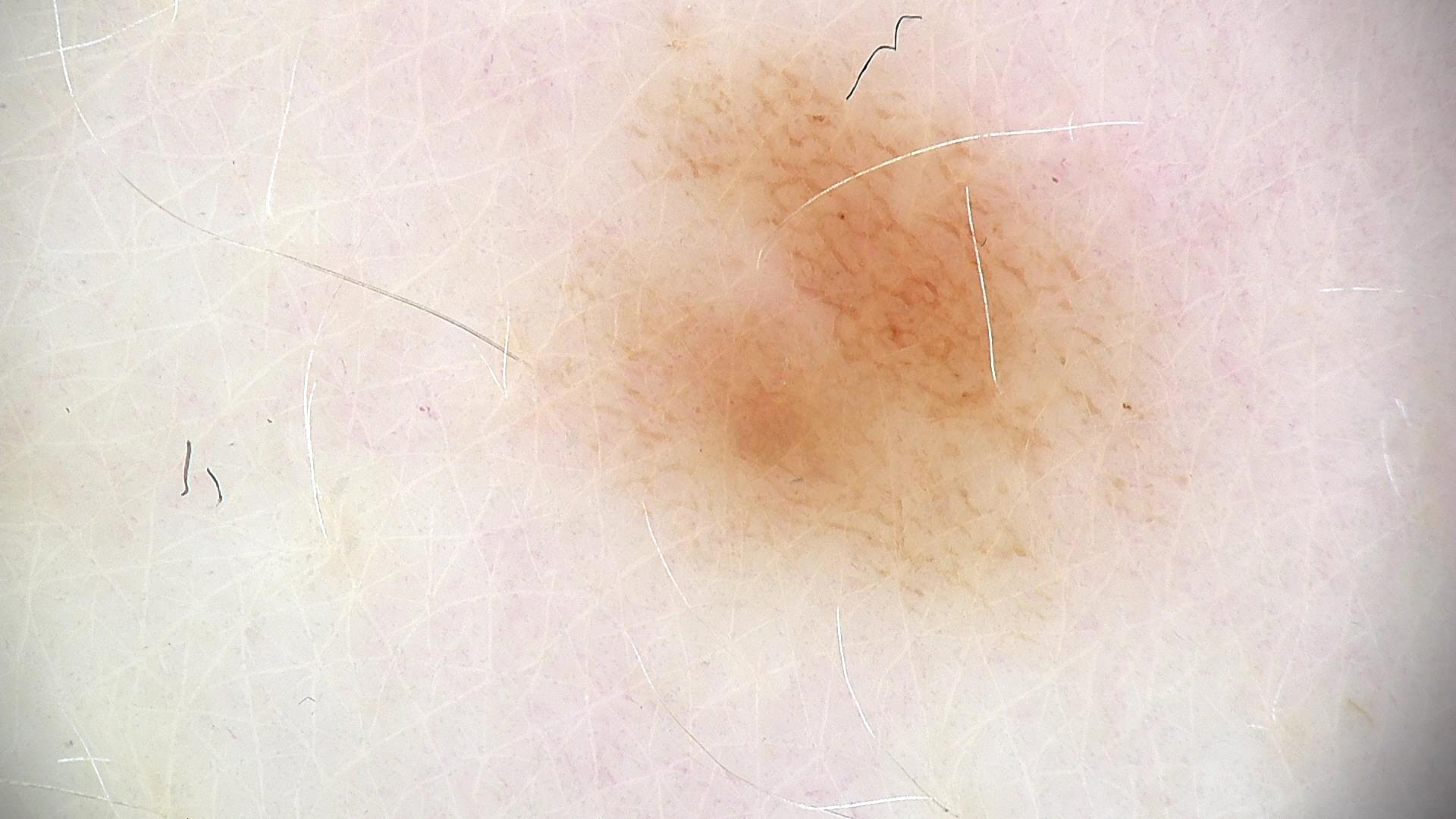– image · dermatoscopy
– subtype · banal
– diagnosis · junctional nevus (expert consensus)